A dermoscopy image of a single skin lesion: 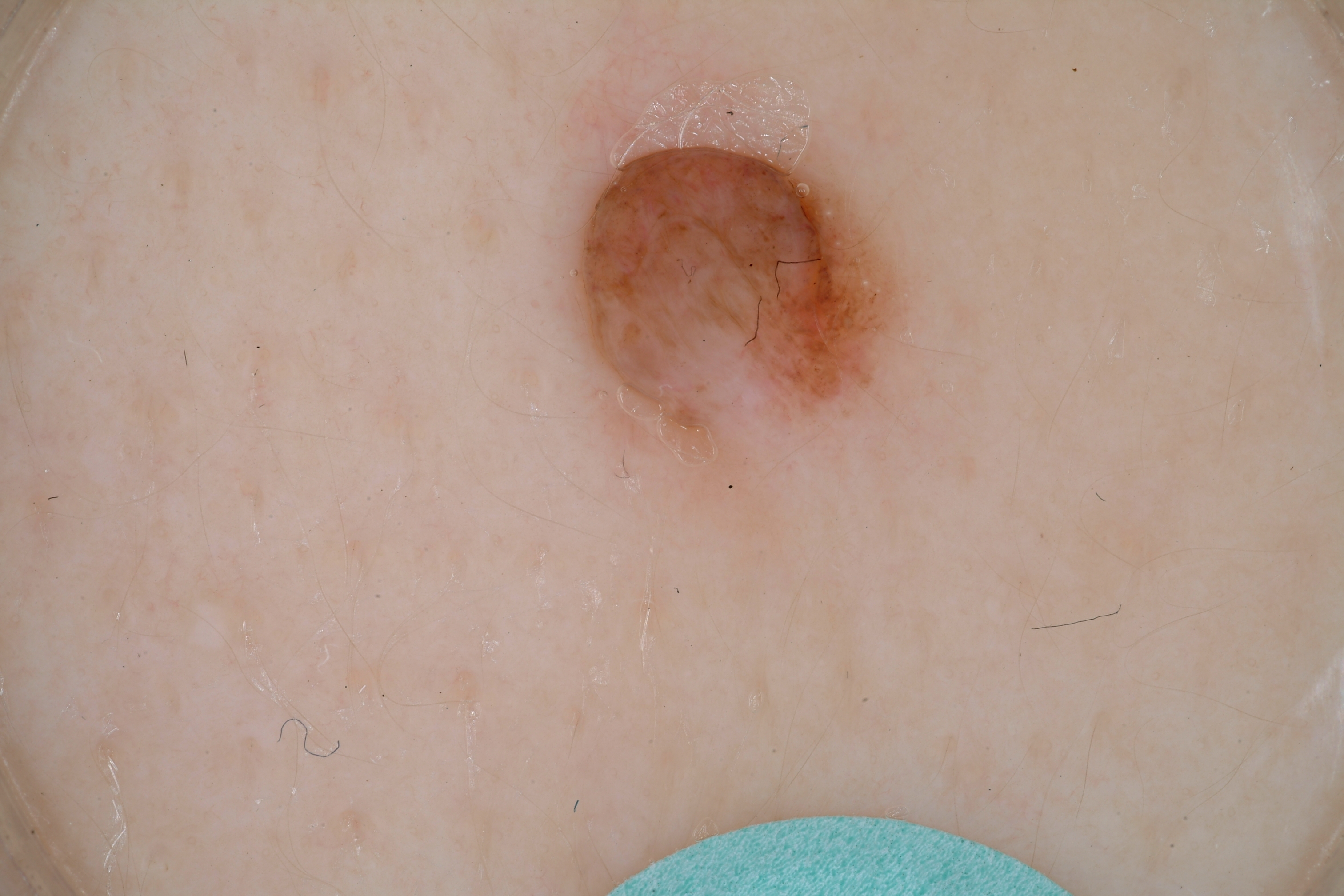dermoscopic pattern = pigment network and milia-like cysts; lesion extent = small; location = 574/139/903/459; diagnosis = a melanocytic nevus.